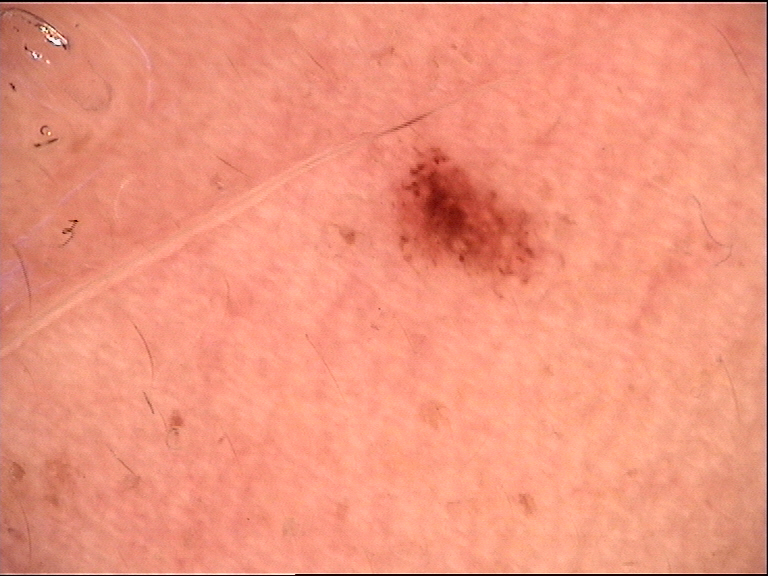Impression:
Consistent with a dysplastic junctional nevus.